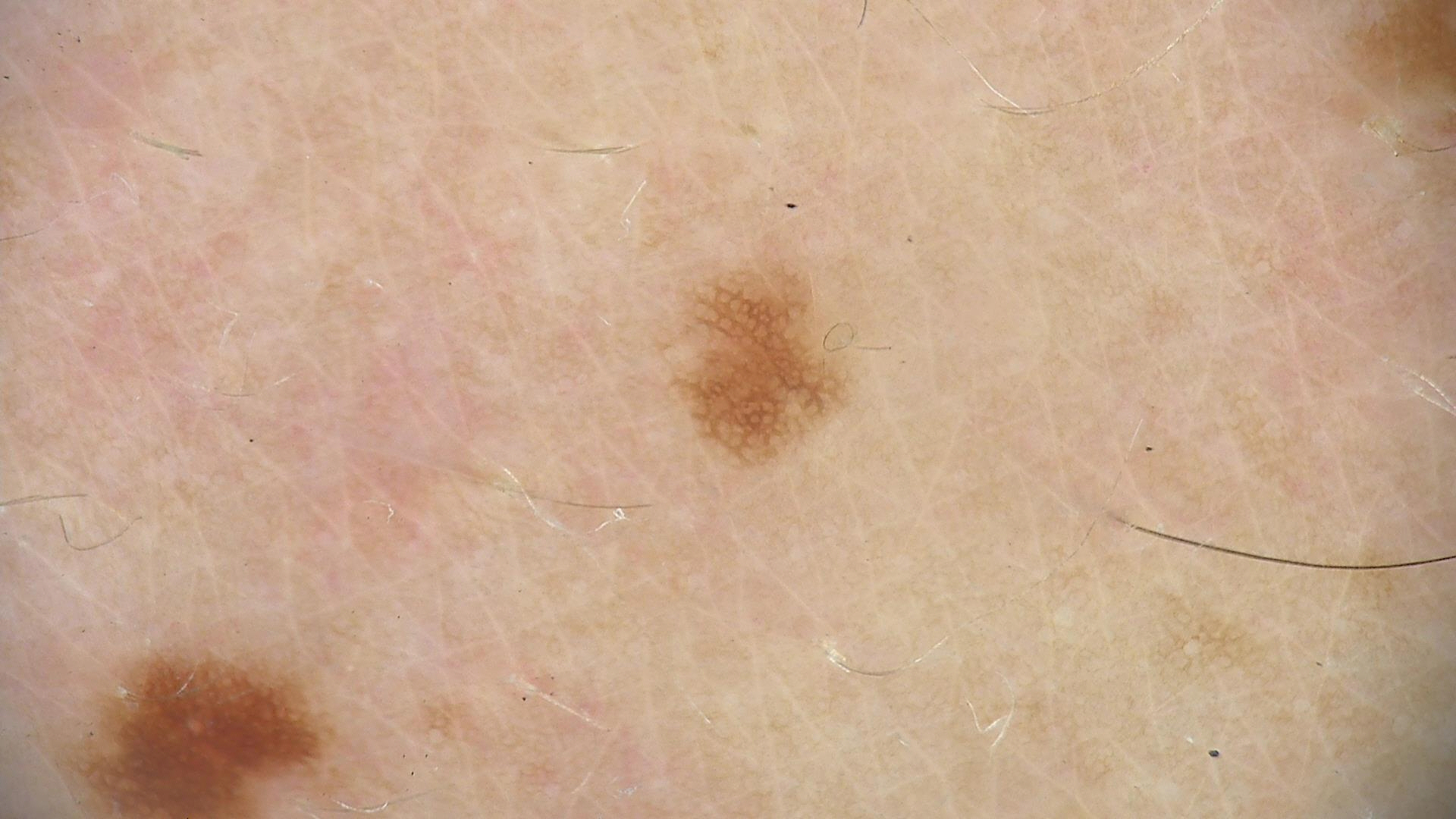A dermatoscopic image of a skin lesion. Consistent with a dysplastic junctional nevus.